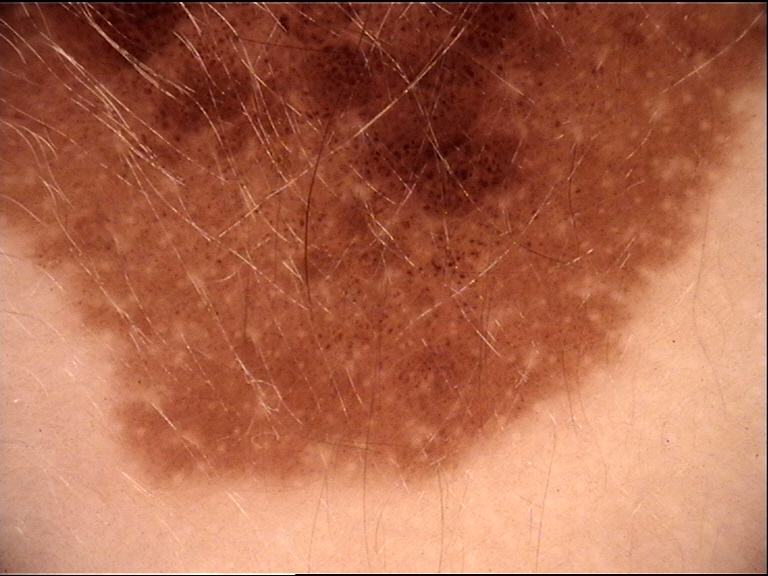<lesion>
  <lesion_type>
    <main_class>banal</main_class>
    <pattern>junctional</pattern>
  </lesion_type>
  <diagnosis>
    <name>congenital junctional nevus</name>
    <code>cjb</code>
    <malignancy>benign</malignancy>
    <super_class>melanocytic</super_class>
    <confirmation>expert consensus</confirmation>
  </diagnosis>
</lesion>